A close-up photograph:
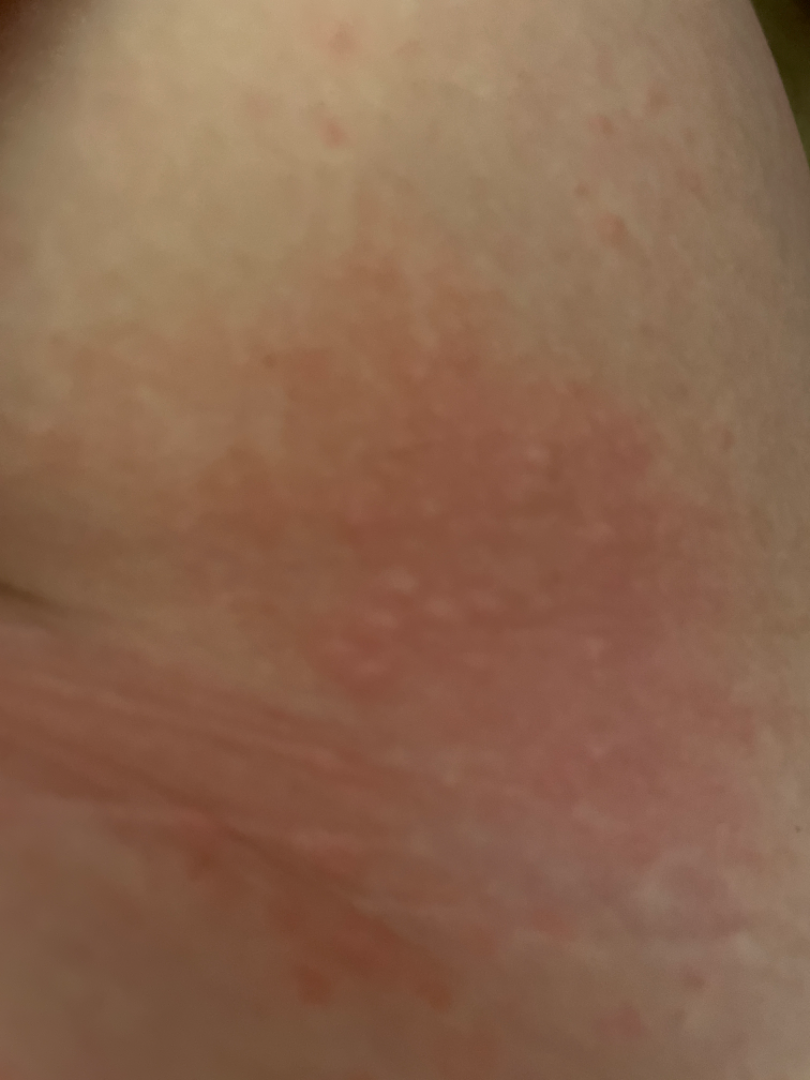Findings:
– diagnostic considerations: the impression was split between Insect Bite and Allergic Contact Dermatitis; less likely is Urticaria